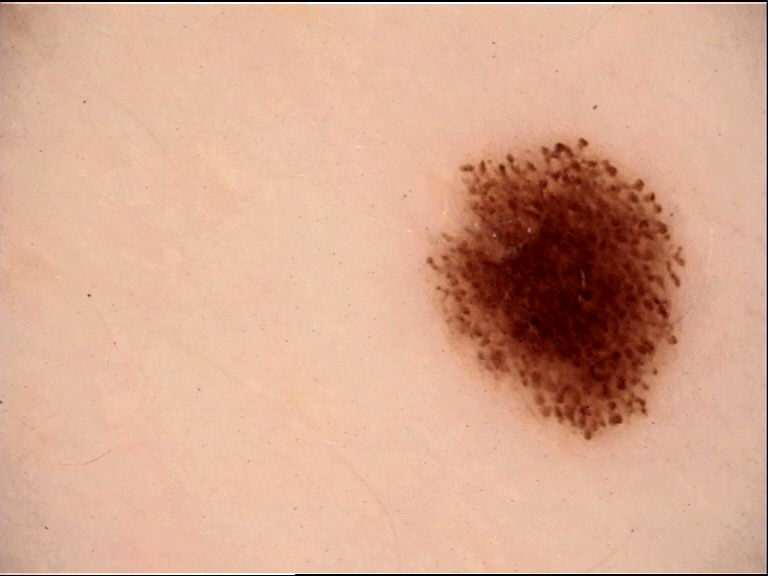Case:
• modality · dermoscopy
• class · dysplastic junctional nevus (expert consensus)